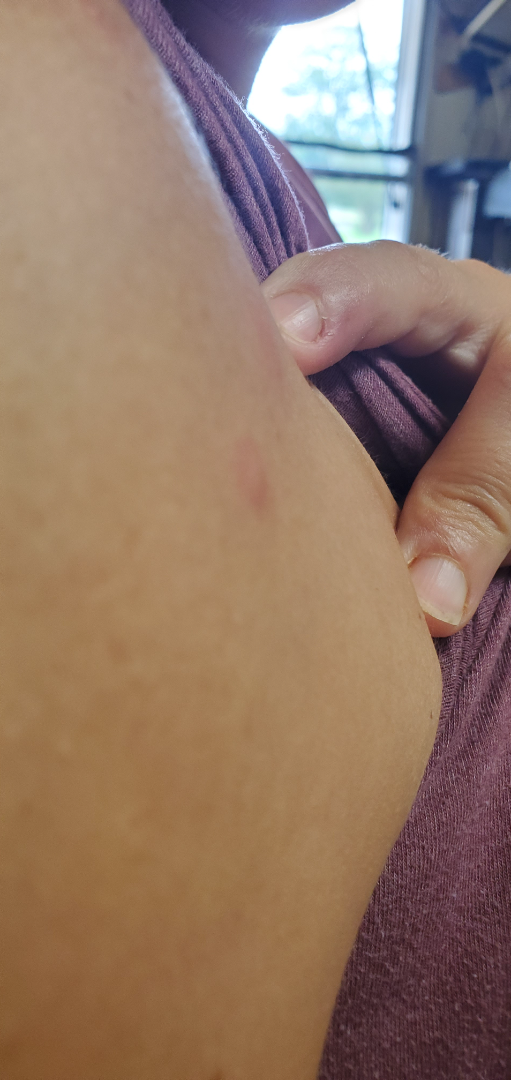Assessment: Diagnostic features were not clearly distinguishable in this photograph. Clinical context: This image was taken at an angle.